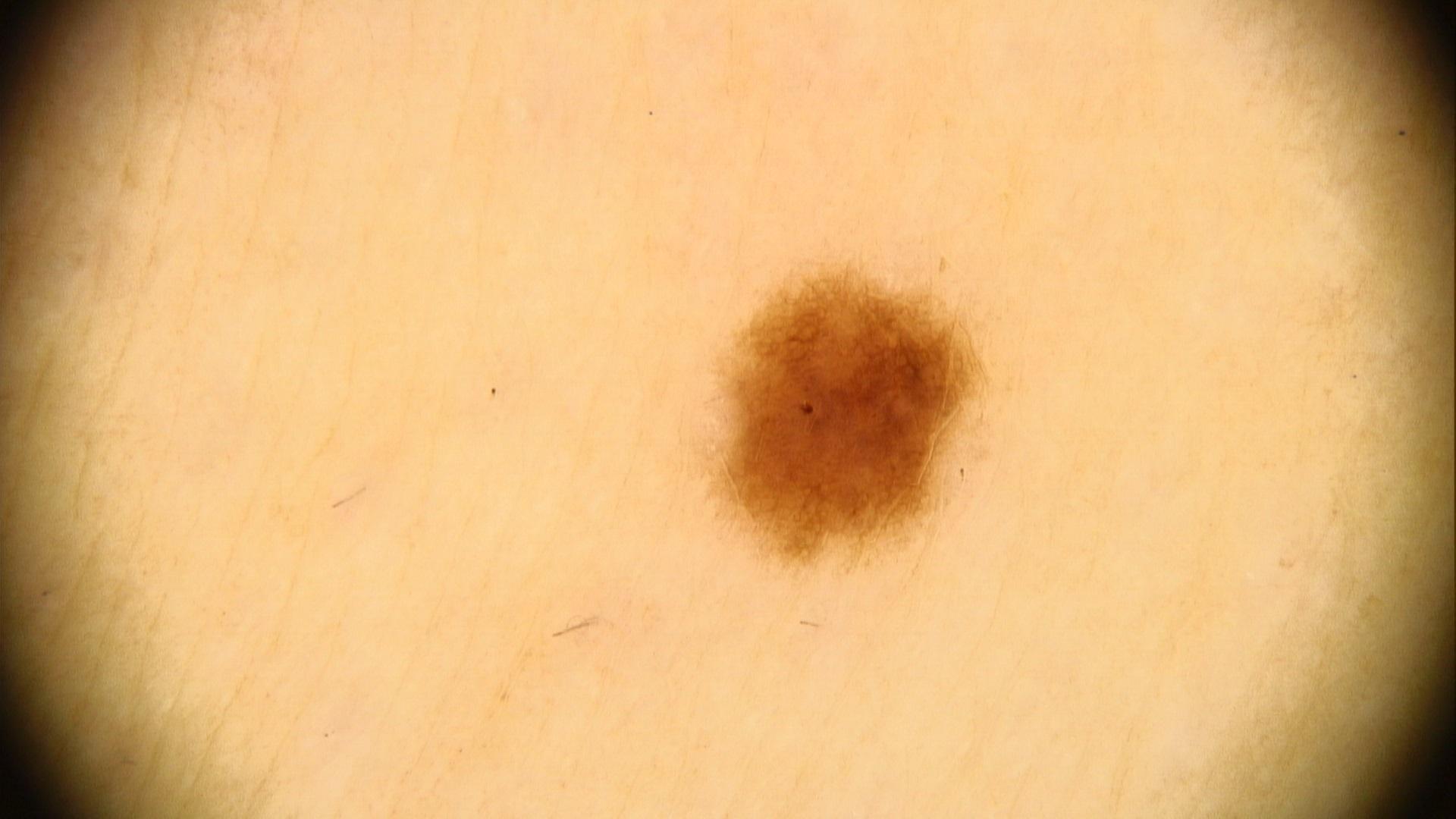diagnosis: Nevus (clinical impression)